The lesion is associated with itching, the photograph is a close-up of the affected area, the patient notes the condition has been present for one to four weeks, the contributor is a male aged 40–49, located on the leg, texture is reported as raised or bumpy.
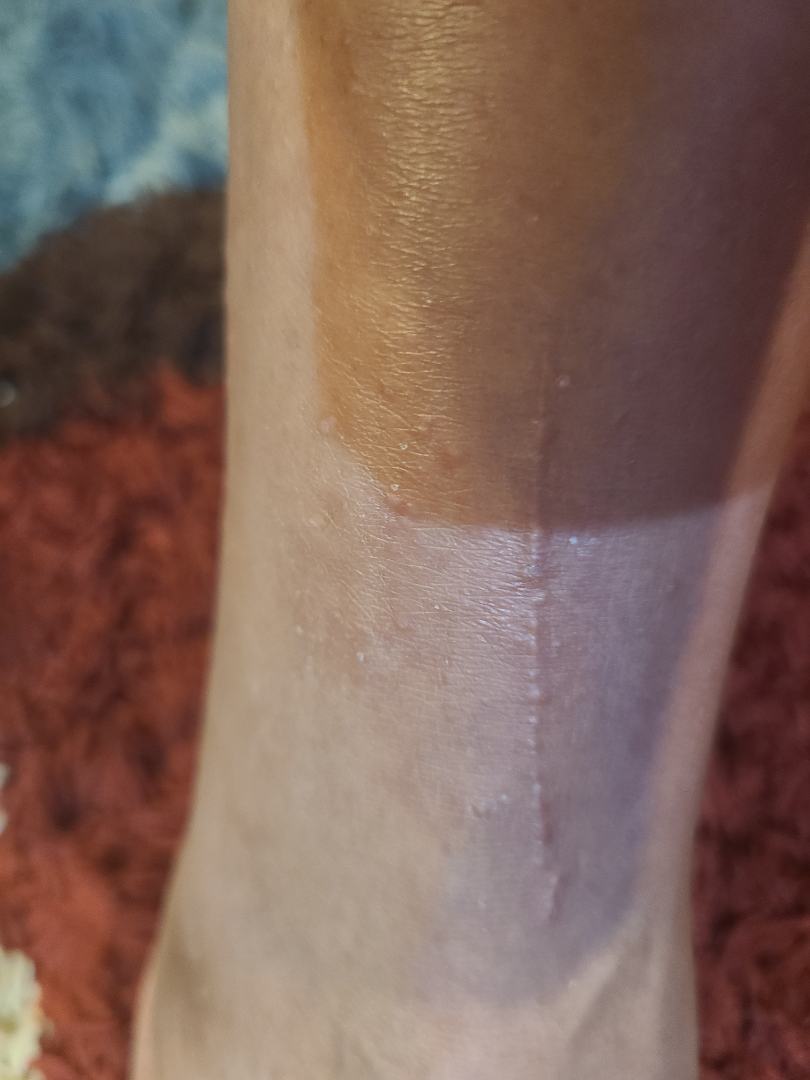The differential includes Lichen planus/lichenoid eruption, Koebner phenomenon and Allergic Contact Dermatitis, with no clear leading consideration; less likely is Lichen nitidus; less probable is Verruca vulgaris.